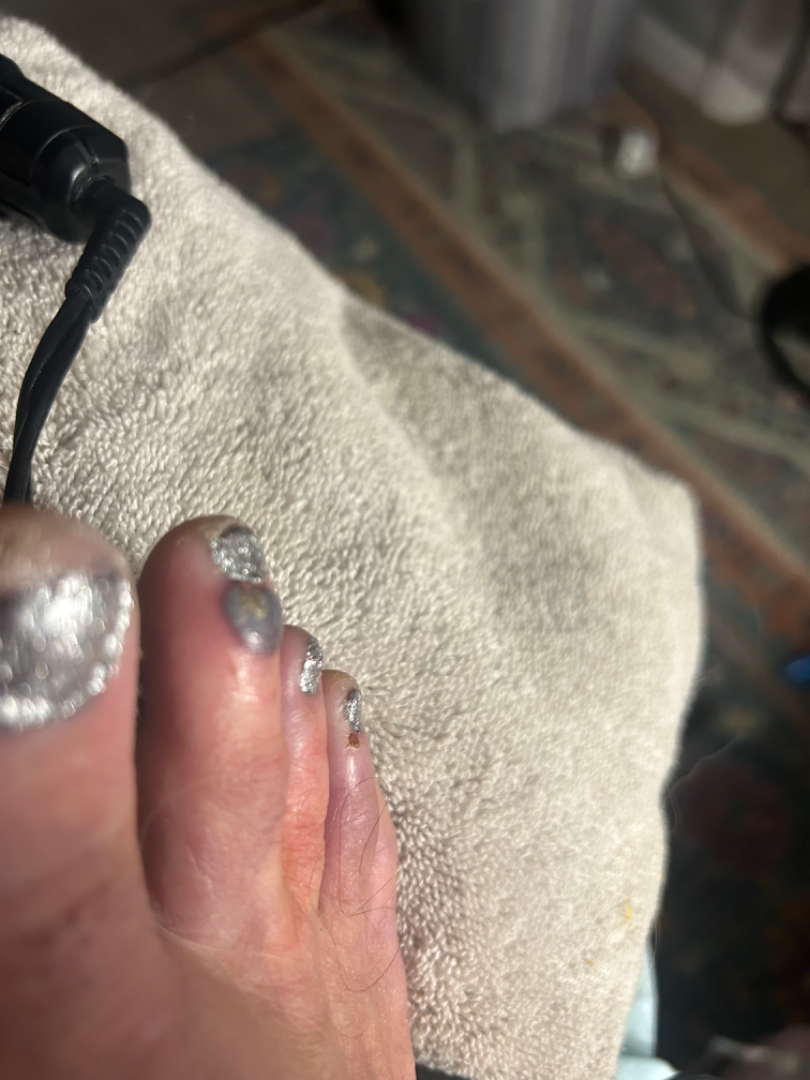{
  "differential": {
    "tied_lead": [
      "Hematoma of skin",
      "Blood blister"
    ],
    "unlikely": [
      "Angiokeratoma of skin",
      "Melanoma"
    ]
  }
}